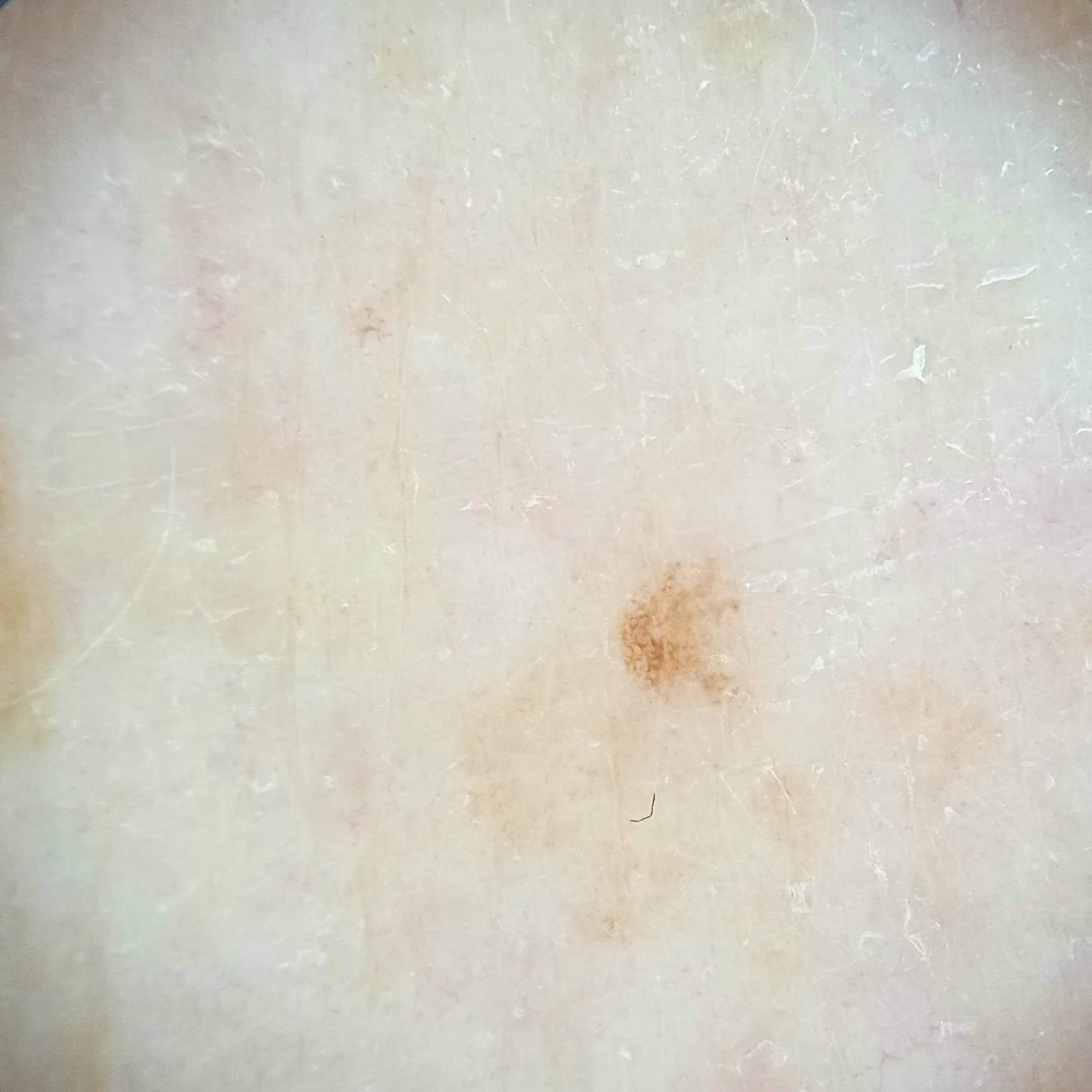Acquired for a research image collection, with no referral diagnosis. A female subject aged 71. Dermoscopy of a skin lesion. Few moles overall by the patient's own estimate. On a questionnaire the patient reported a personal history of skin cancer and a personal history of cancer. The lesion is on an arm. The lesion measures approximately 1.7 mm. The diagnostic impression was a melanocytic nevus.